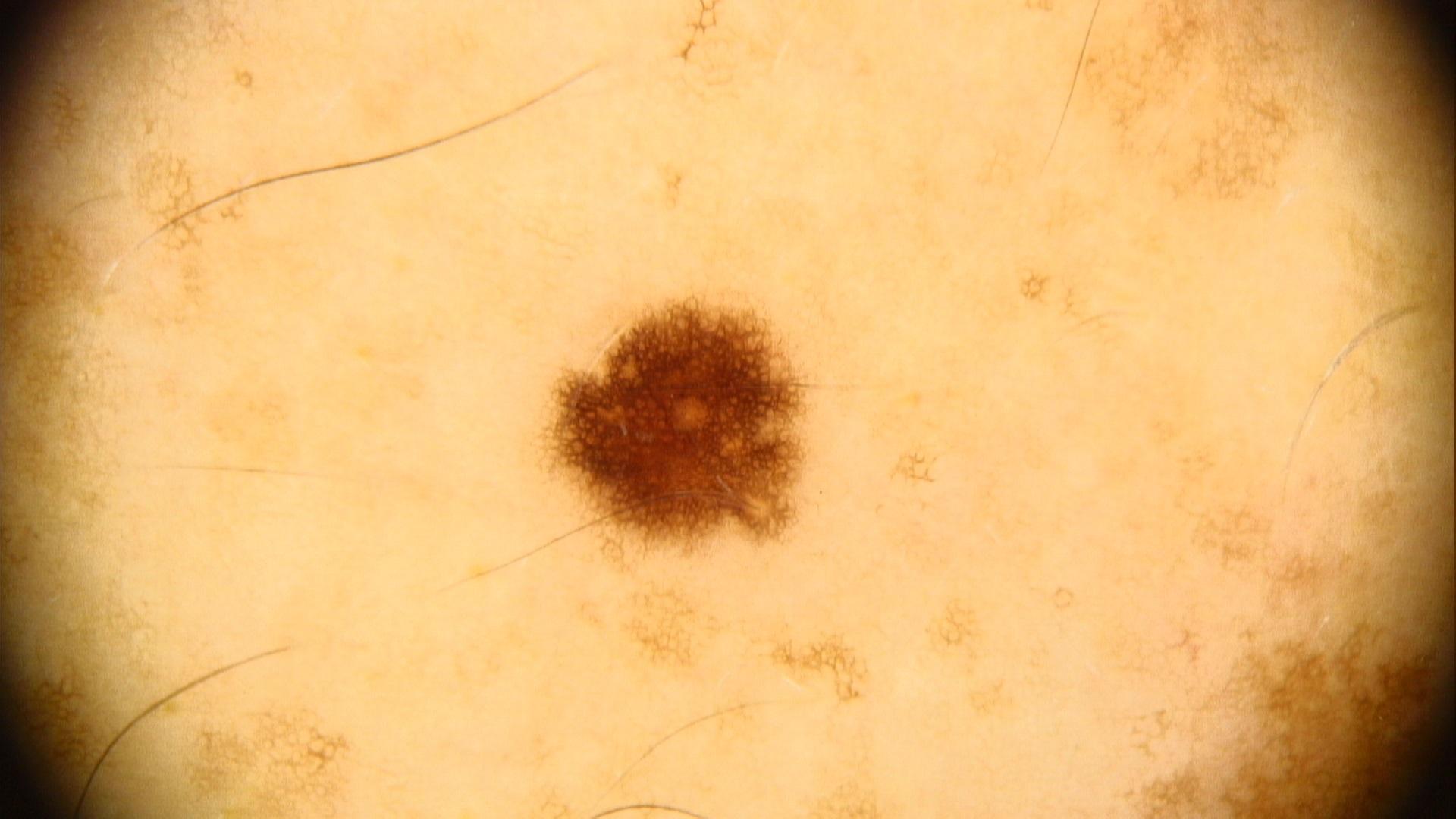modality = dermoscopic image | skin phototype = III | subject = male, roughly 40 years of age | location = the trunk, specifically the posterior trunk | diagnosis = Nevus (clinical impression).